This image was taken at a distance; the back of the torso, leg, front of the torso and head or neck are involved: 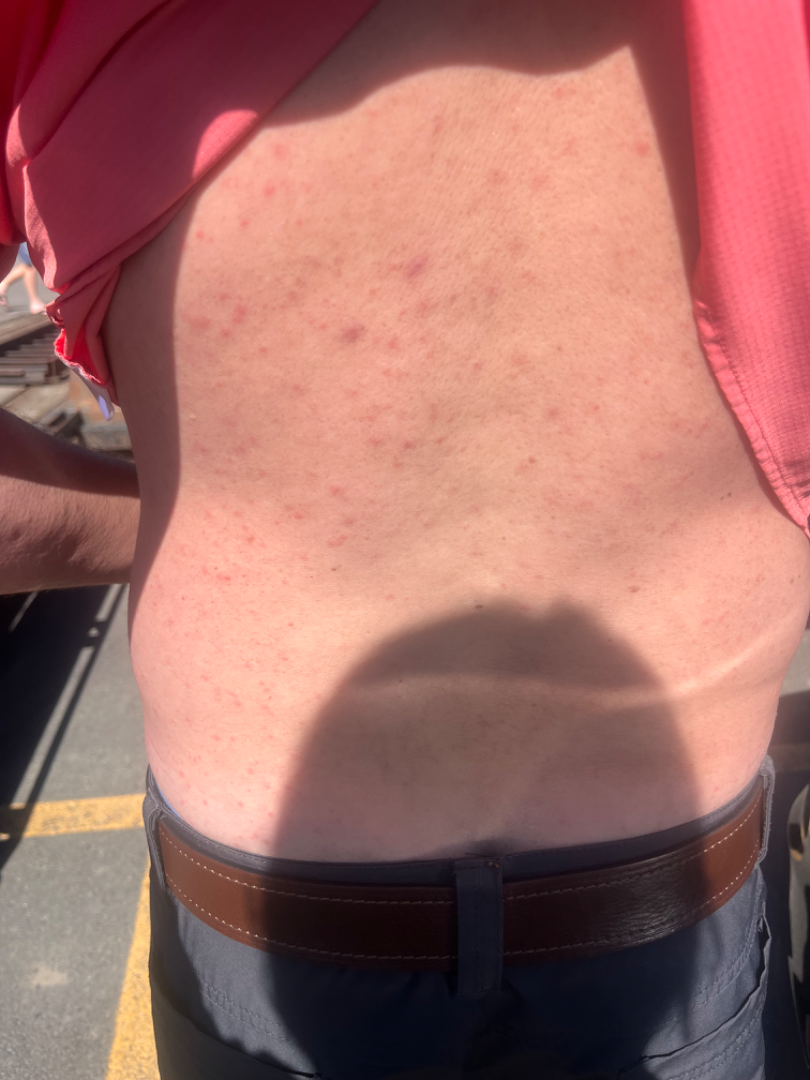Q: What was the assessment?
A: not assessable